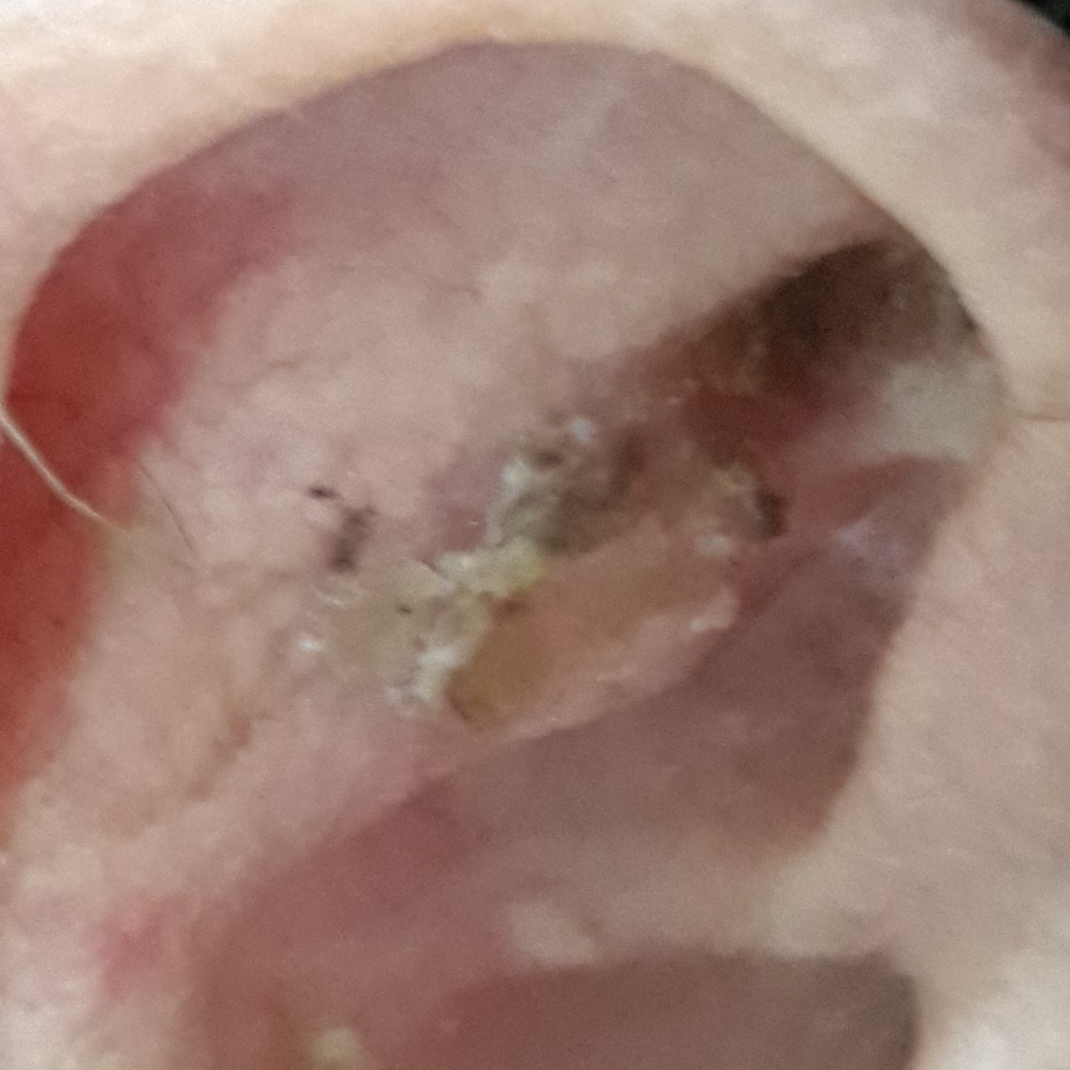Q: Who is the patient?
A: aged 78
Q: How was this image acquired?
A: clinical photograph
Q: Any reported symptoms?
A: change in appearance, elevation, itching, pain
Q: What is this lesion?
A: seborrheic keratosis (clinical consensus)